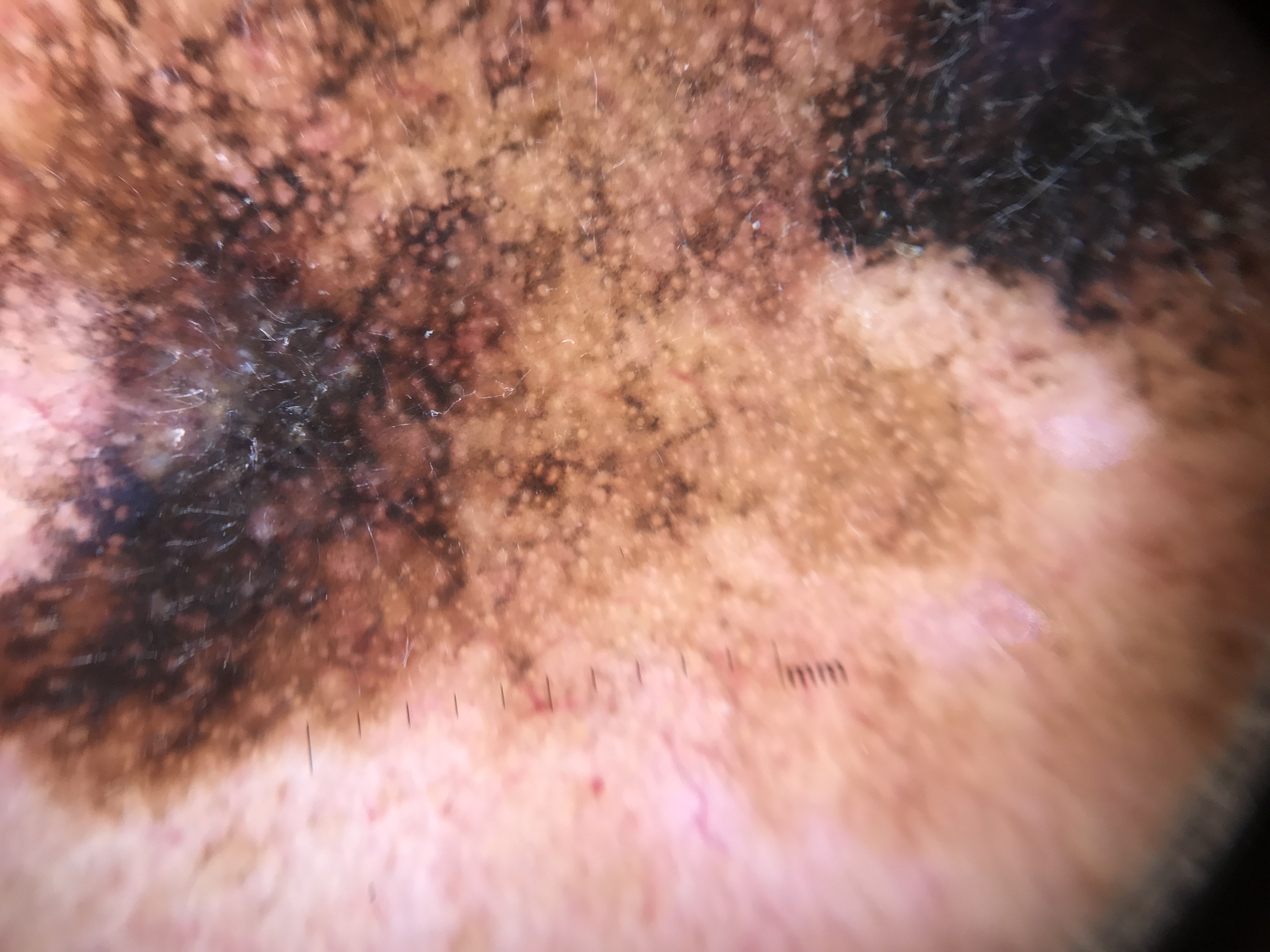Confirmed on histopathology as a lentigo maligna.